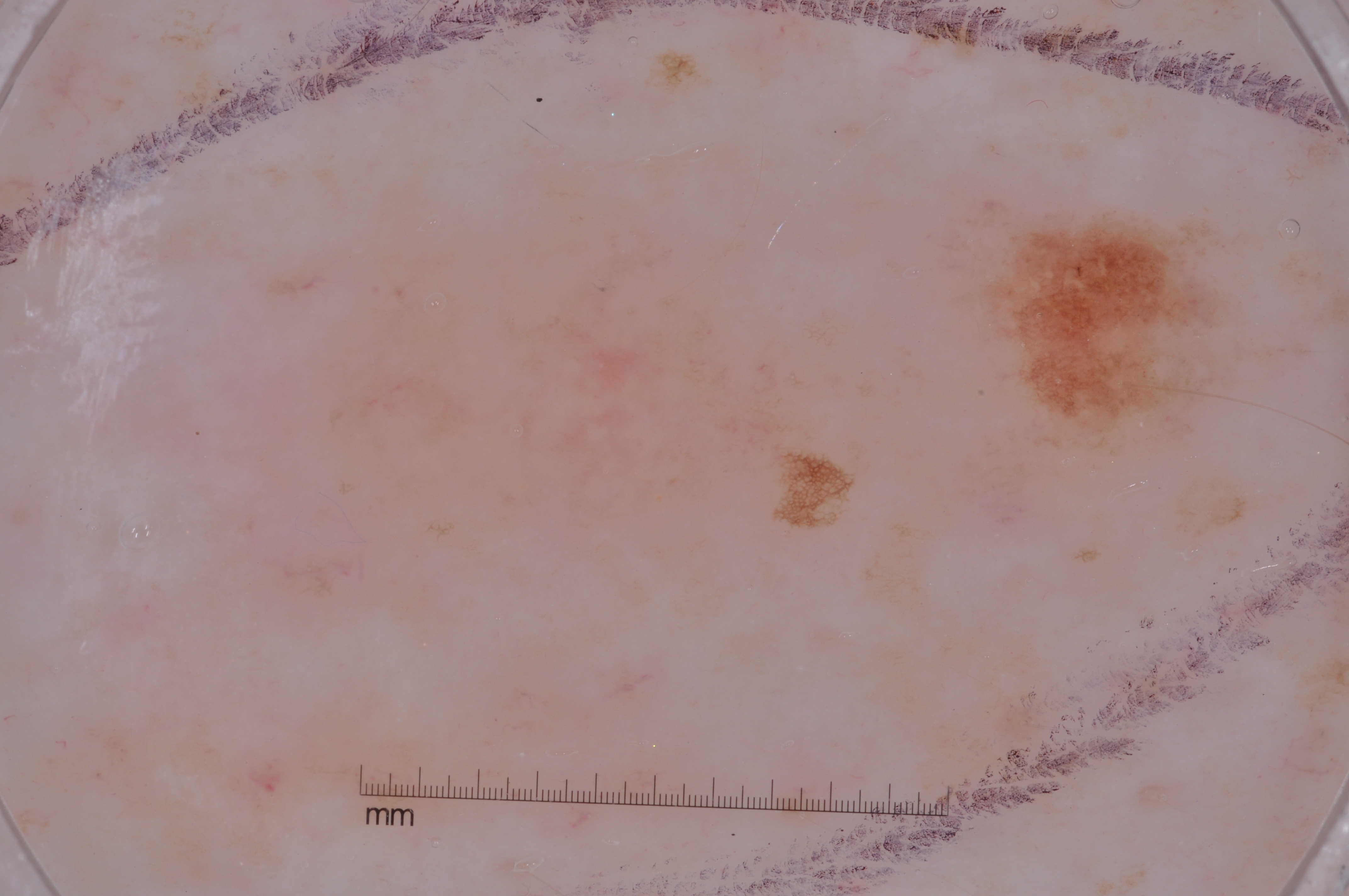This is a dermoscopic photograph of a skin lesion.
A male patient, aged 58 to 62.
The lesion spans x1=980 y1=214 x2=1218 y2=449.
The dermoscopic pattern shows pigment network.
Consistent with a melanocytic nevus.